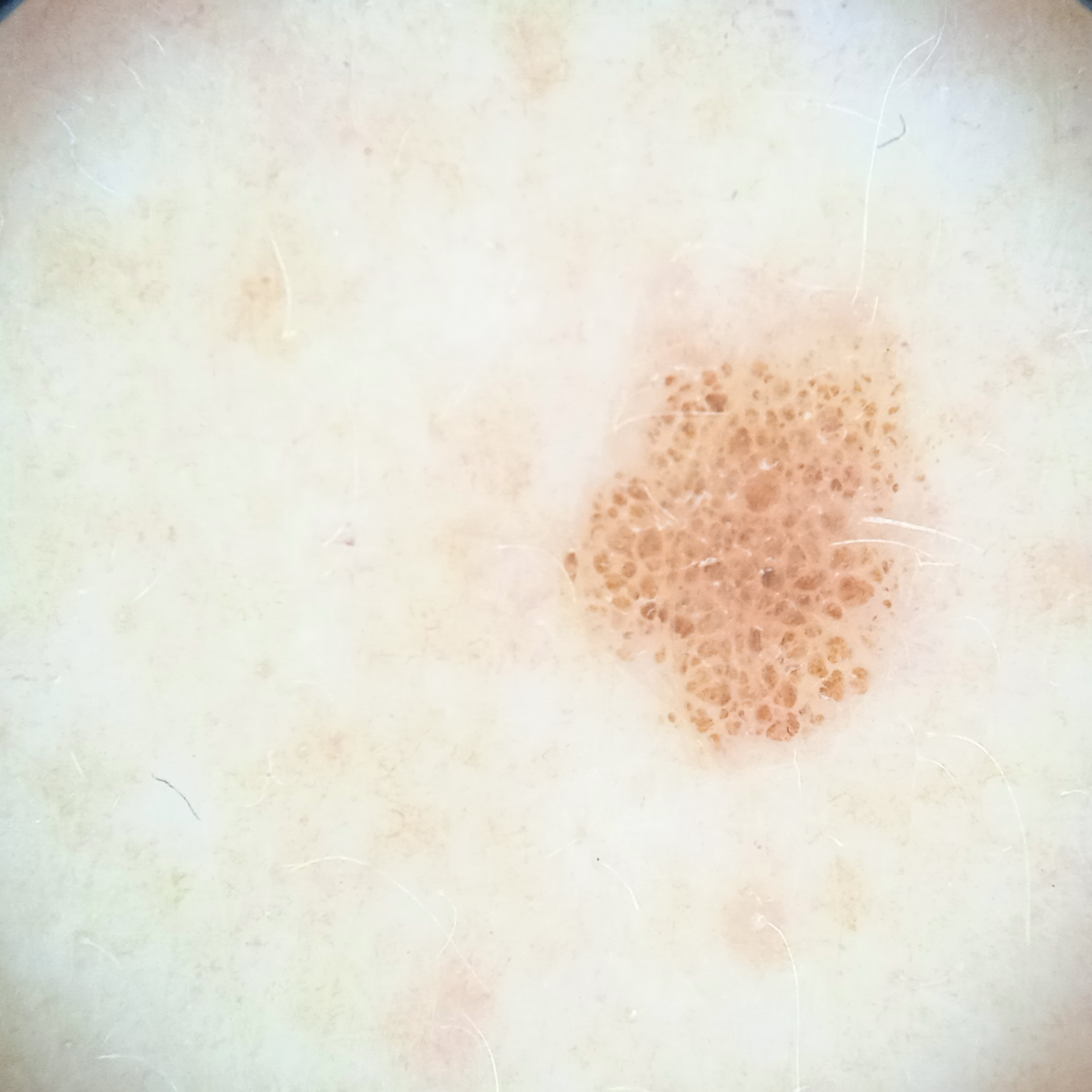diagnostic label = melanocytic nevus (dermatologist consensus).